A dermoscopic close-up of a skin lesion.
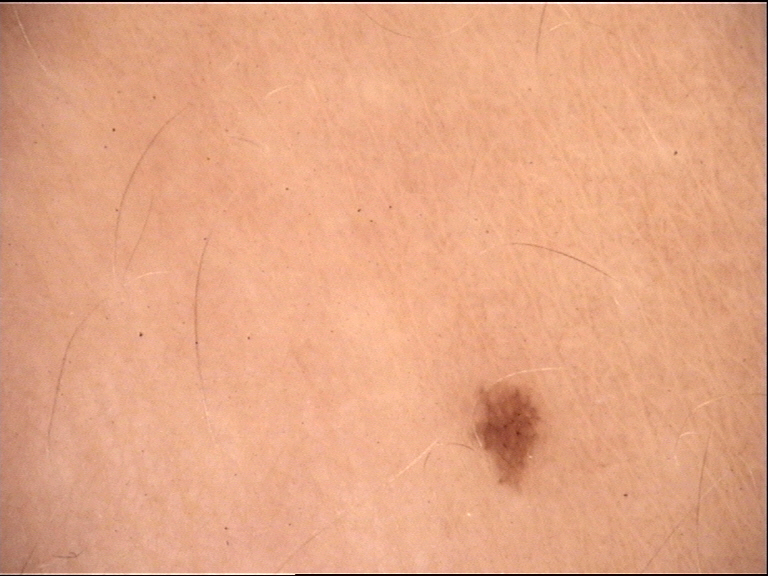Findings: The morphology is that of a banal lesion. Impression: The diagnostic label was a junctional nevus.